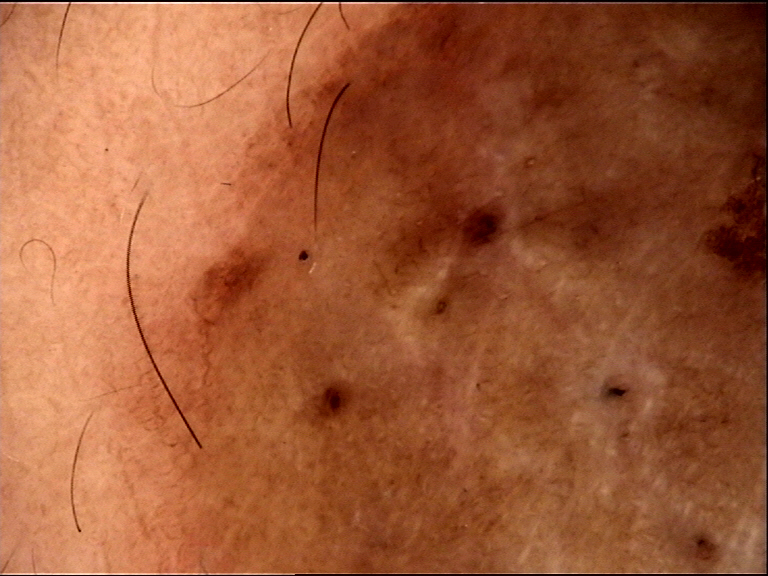<case>
<lesion_type>
<main_class>banal</main_class>
<pattern>compound</pattern>
</lesion_type>
<diagnosis>
<name>congenital compound nevus</name>
<code>ccb</code>
<malignancy>benign</malignancy>
<super_class>melanocytic</super_class>
<confirmation>expert consensus</confirmation>
</diagnosis>
</case>